An image taken at a distance · the lesion involves the leg and arm — 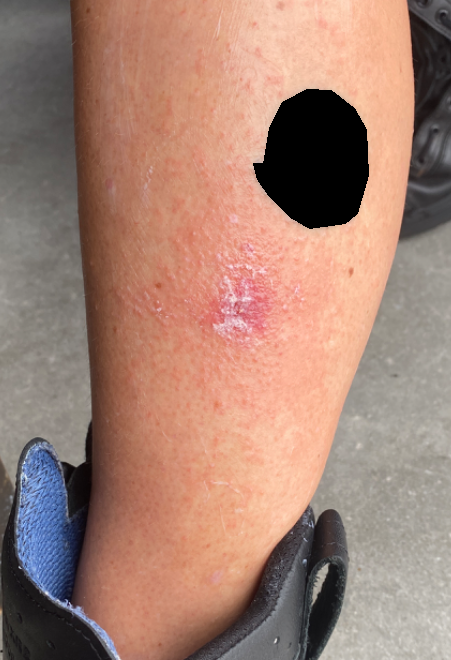| key | value |
|---|---|
| differential | the impression was split between Impetigo and Allergic Contact Dermatitis |